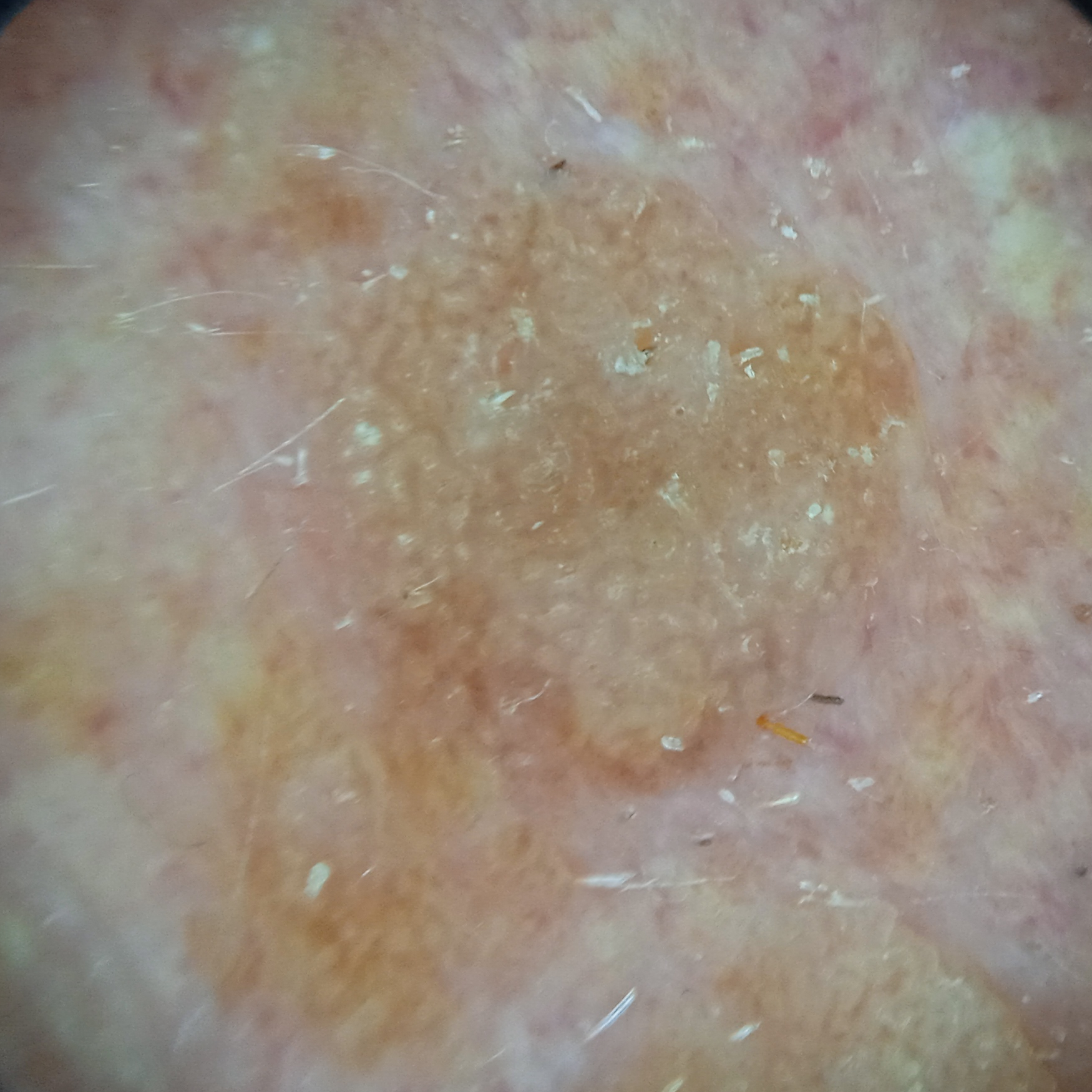Case:
• nevus count: few melanocytic nevi overall
• clinical context: research study (no referral diagnosis)
• image type: dermoscopic image
• lesion size: 7.5 mm
• diagnostic label: seborrheic keratosis (dermatologist consensus)